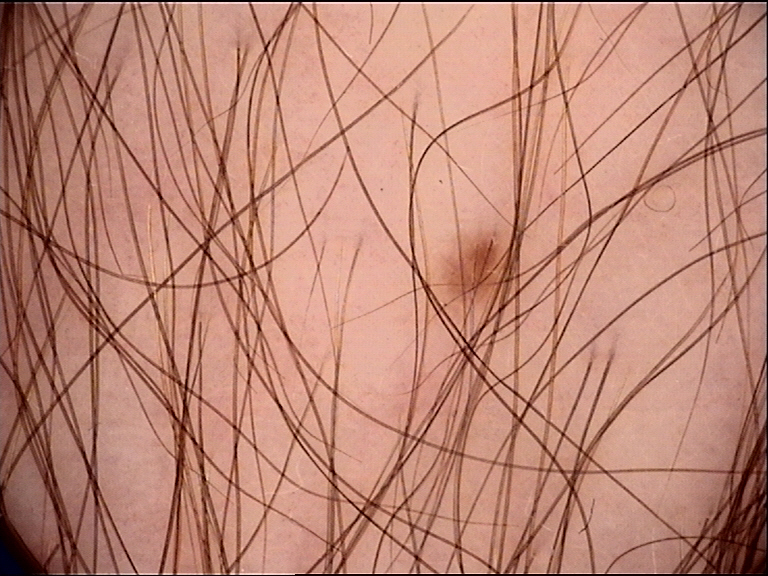The morphology is that of a banal lesion. Labeled as a junctional nevus.